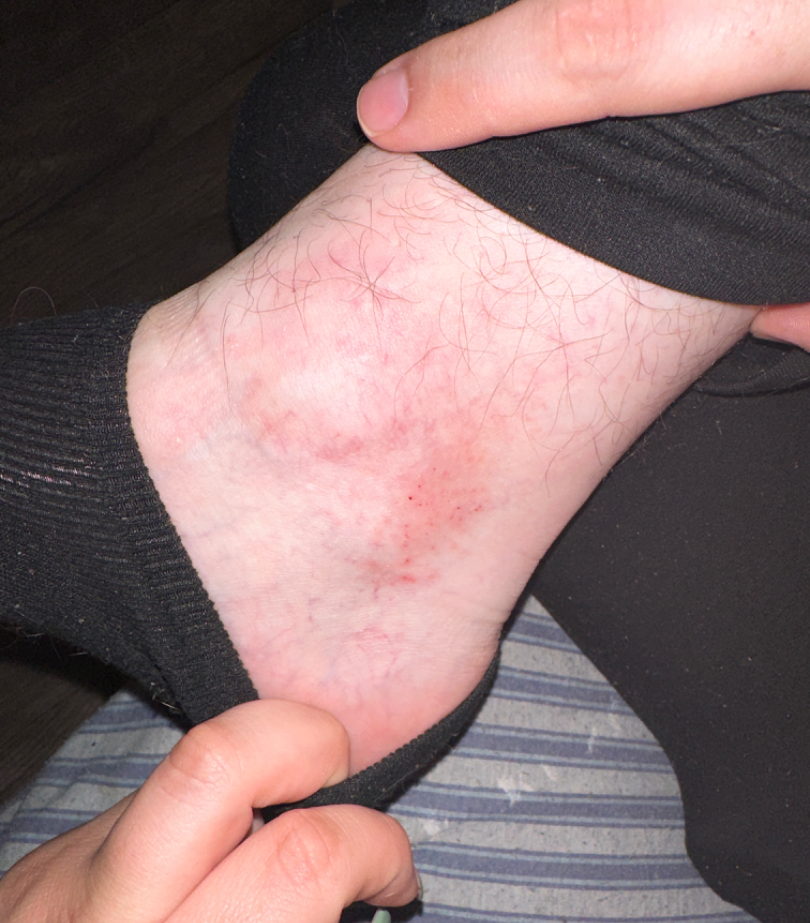view = at an angle
affected area = top or side of the foot
subject = male, age 18–29
diagnostic considerations = the primary impression is Eczema; the differential also includes Irritant Contact Dermatitis; less likely is Stasis Dermatitis; less probable is Allergic Contact Dermatitis